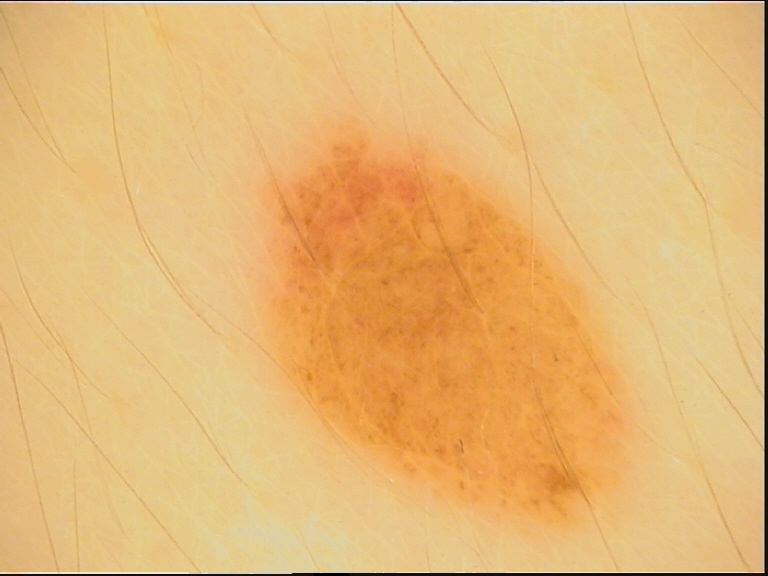modality: dermoscopy | diagnosis: compound nevus (expert consensus).